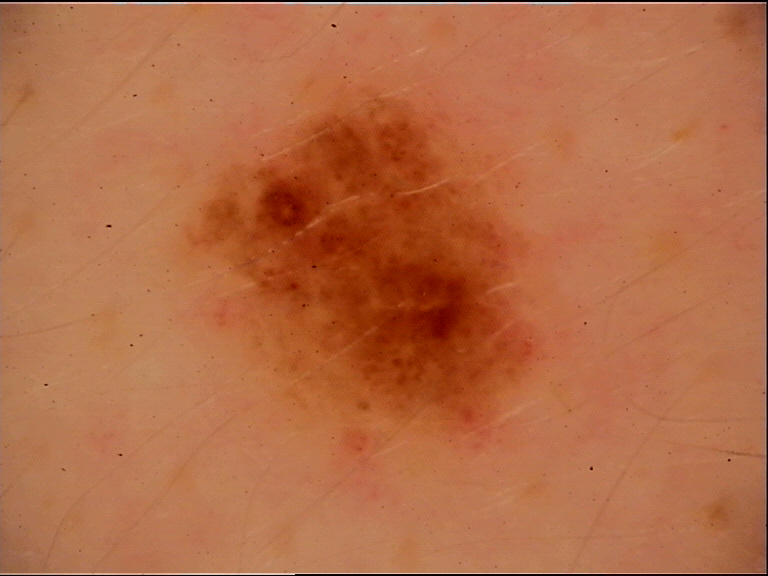Conclusion:
Consistent with a benign lesion — a dysplastic junctional nevus.